This is a dermoscopic photograph of a skin lesion: 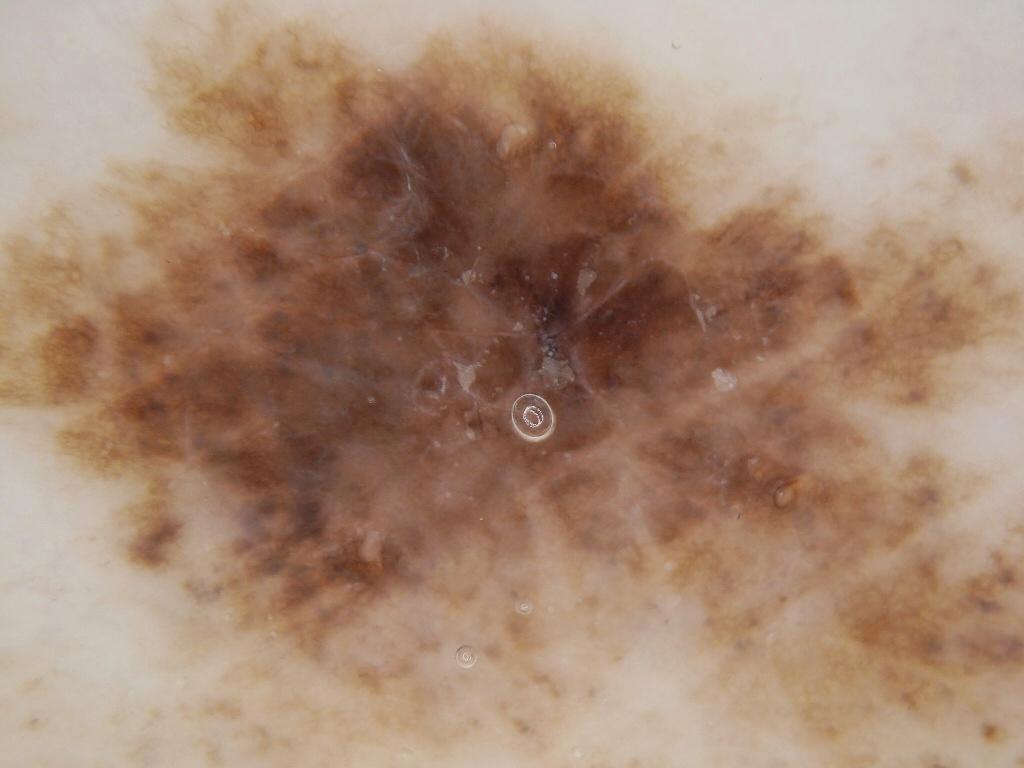The lesion stretches across essentially the whole frame.
Histopathological examination showed a malignant lesion.